The patient says their skin reddens with sun exposure; a dermoscopic image of a skin lesion; by self-report, a personal history of cancer and a family history of skin cancer; the patient describes having few moles overall; referred with a clinical suspicion of basal cell carcinoma; a male patient age 81: 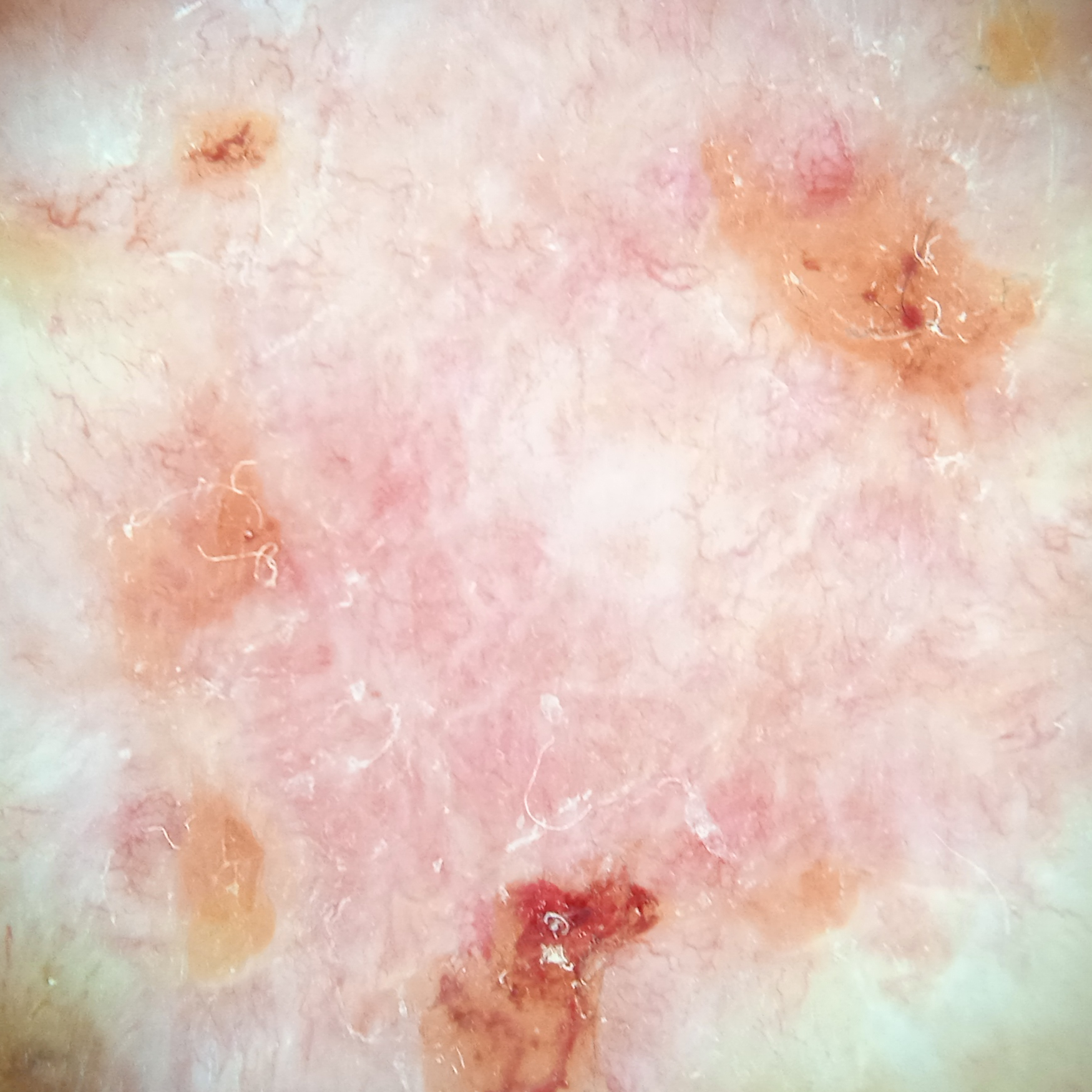• anatomic site — the back
• lesion size — 12.6 mm
• diagnostic label — basal cell carcinoma (biopsy-proven)